This is a dermoscopic photograph of a skin lesion:
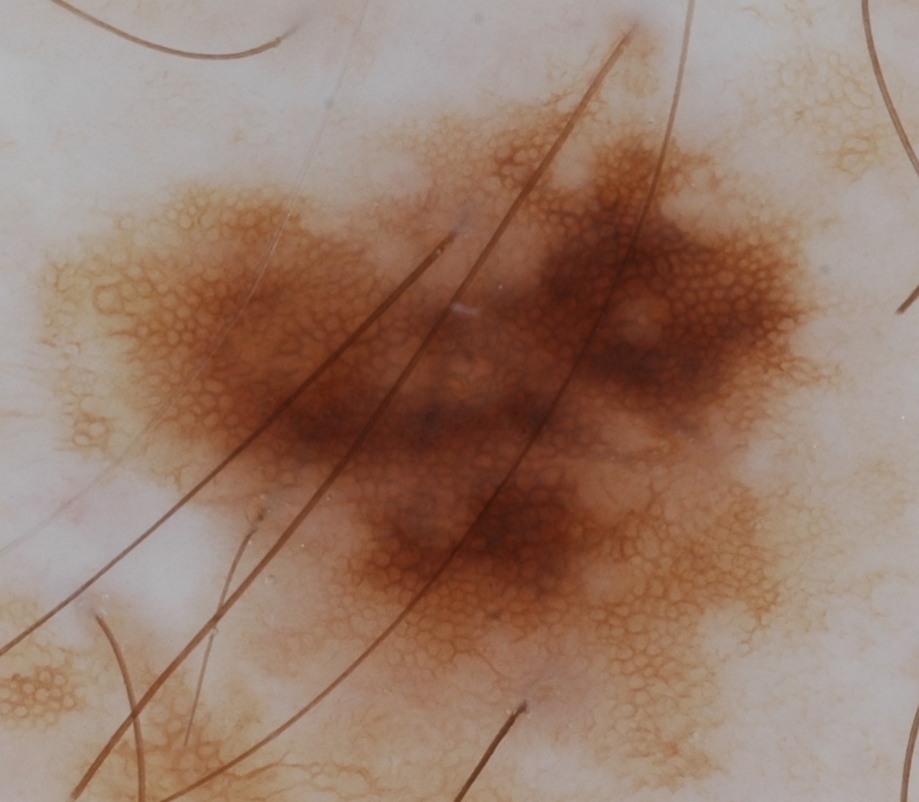| field | value |
|---|---|
| dermoscopic pattern | pigment network |
| field coverage | spans the dermoscopic field |
| assessment | a melanocytic nevus |